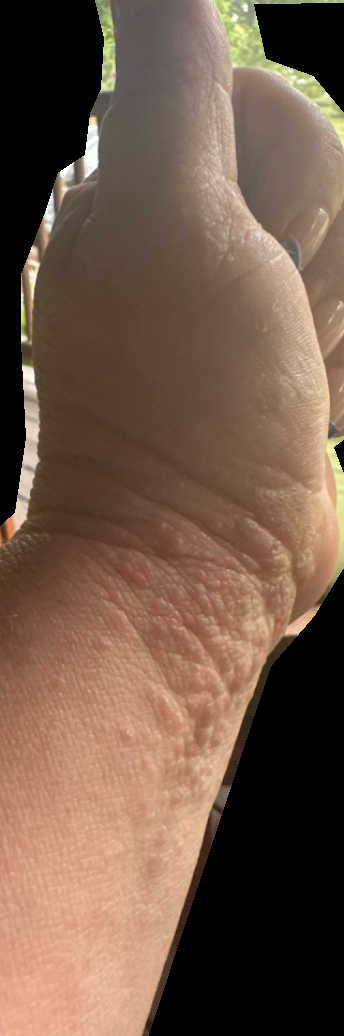photo taken: at an angle | history: one to three months | self-categorized as: a rash | reported symptoms: itching and burning | differential: Allergic Contact Dermatitis (primary); Eczema (considered).